Per the chart, a prior melanoma but no melanoma in first-degree relatives · a dermatoscopic image of a skin lesion — 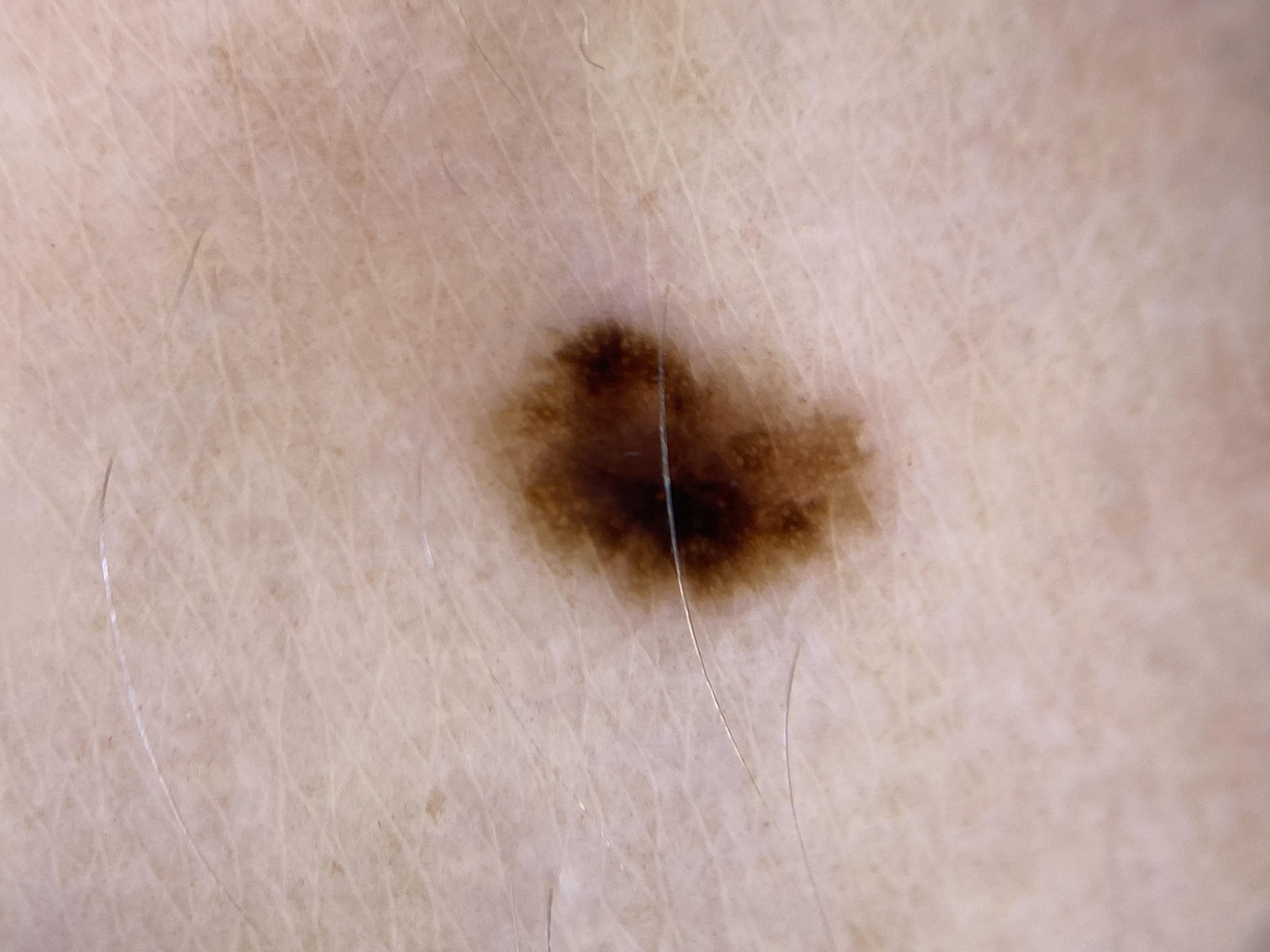{
  "lesion_location": {
    "region": "a lower extremity"
  },
  "diagnosis": {
    "name": "Nevus",
    "malignancy": "benign",
    "confirmation": "histopathology",
    "lineage": "melanocytic"
  }
}